The contributor is 18–29, female · the photograph was taken at a distance — 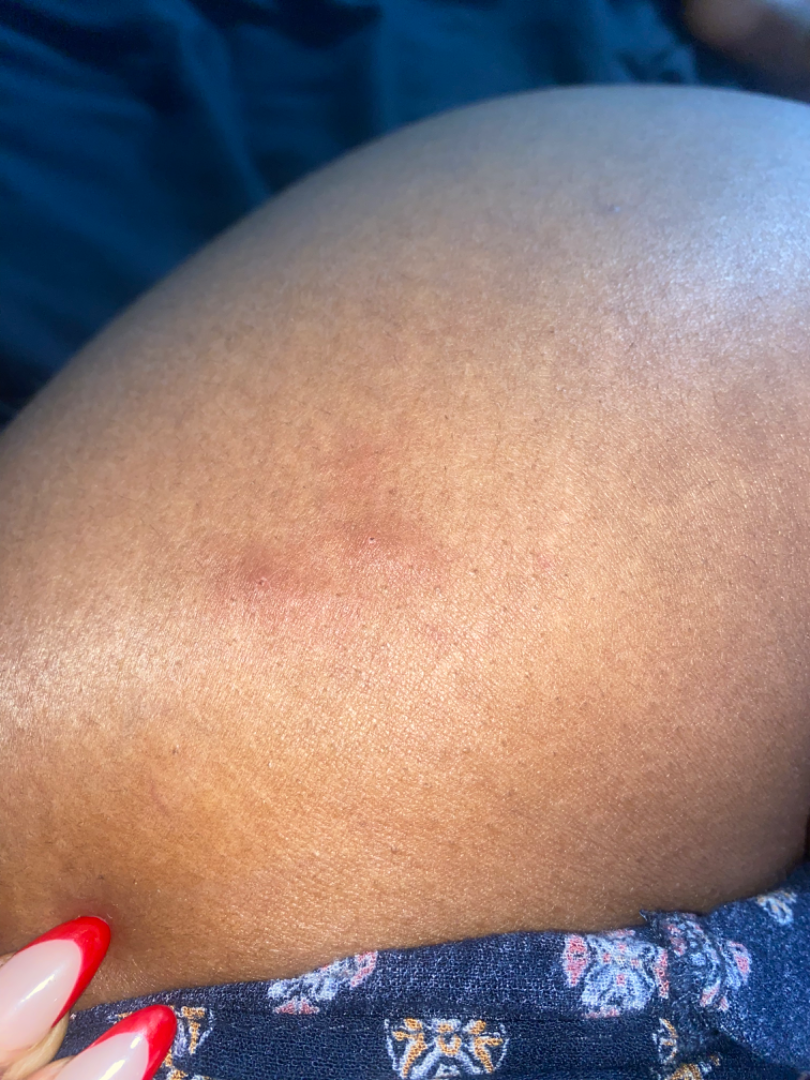Insect Bite and Cyst were each considered, in no particular order; a more distant consideration is Adnexal neoplasm; lower on the differential is Urticaria; less probable is Eczema.